A close-up photograph, the affected area is the leg.
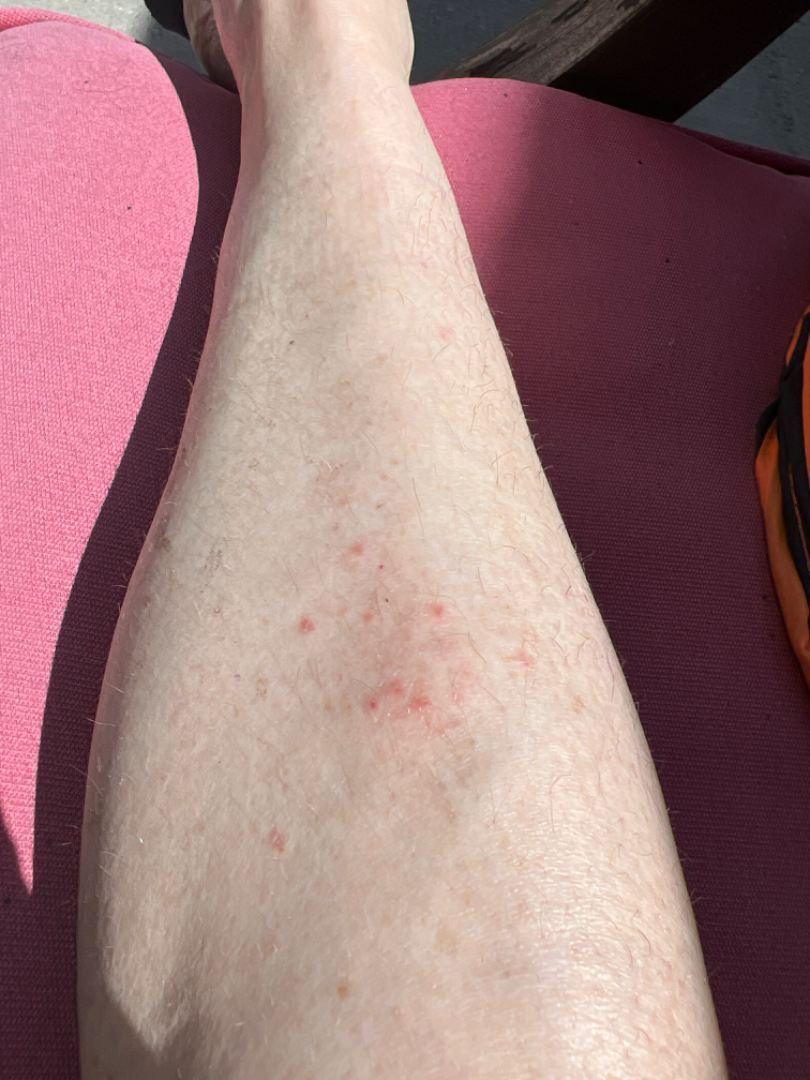assessment — the impression was split between Eczema and Stasis Dermatitis; a remote consideration is Folliculitis.